A skin lesion imaged with a dermatoscope · the patient is a male aged approximately 35.
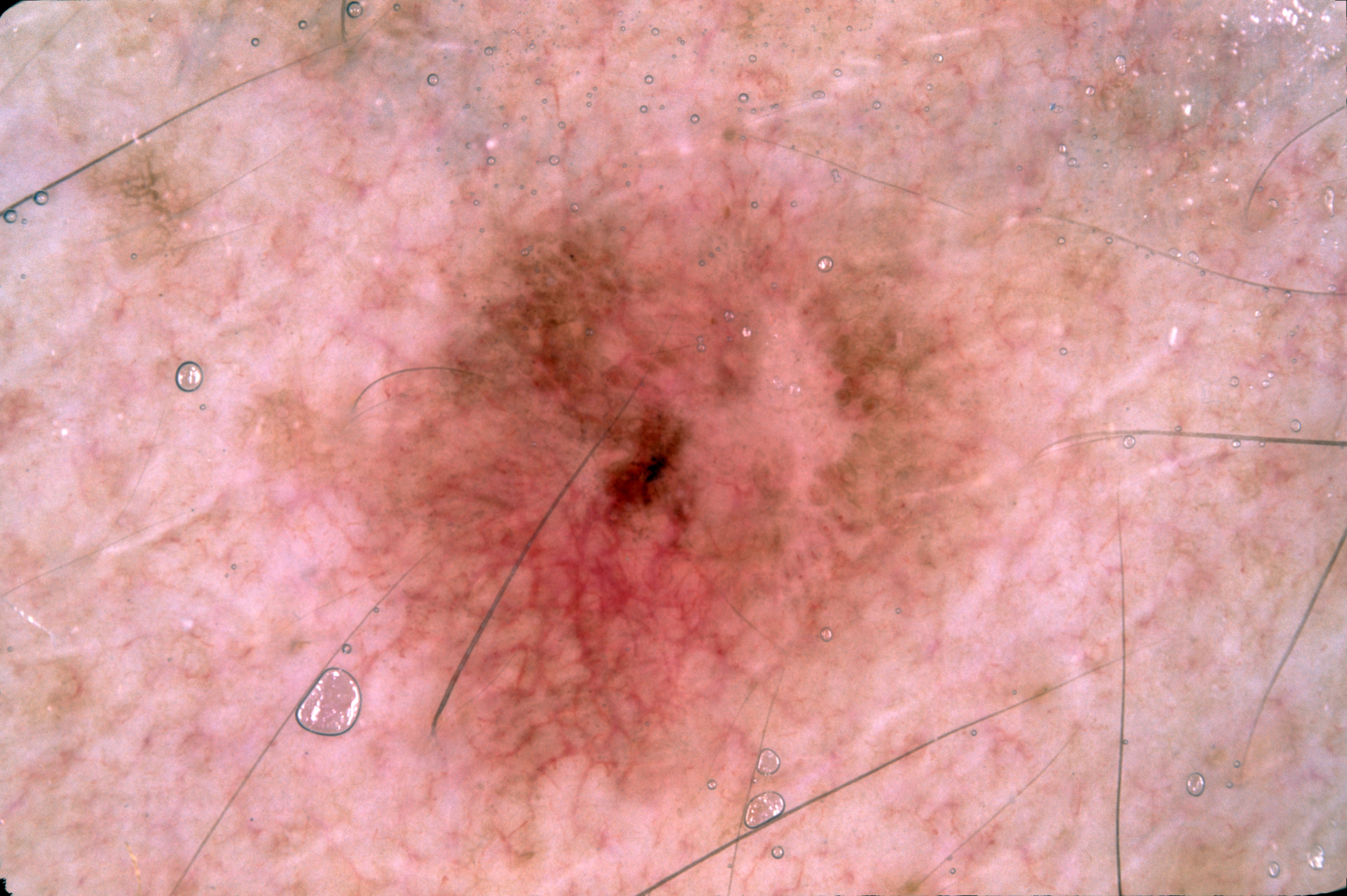Findings:
On dermoscopy, the lesion shows negative network. A mid-sized lesion within the field. The lesion is bounded by x1=305 y1=175 x2=999 y2=798.
Diagnosis:
Histopathologically confirmed as a melanoma, a malignant skin lesion.